A close-up photograph · the head or neck, leg and top or side of the foot are involved:
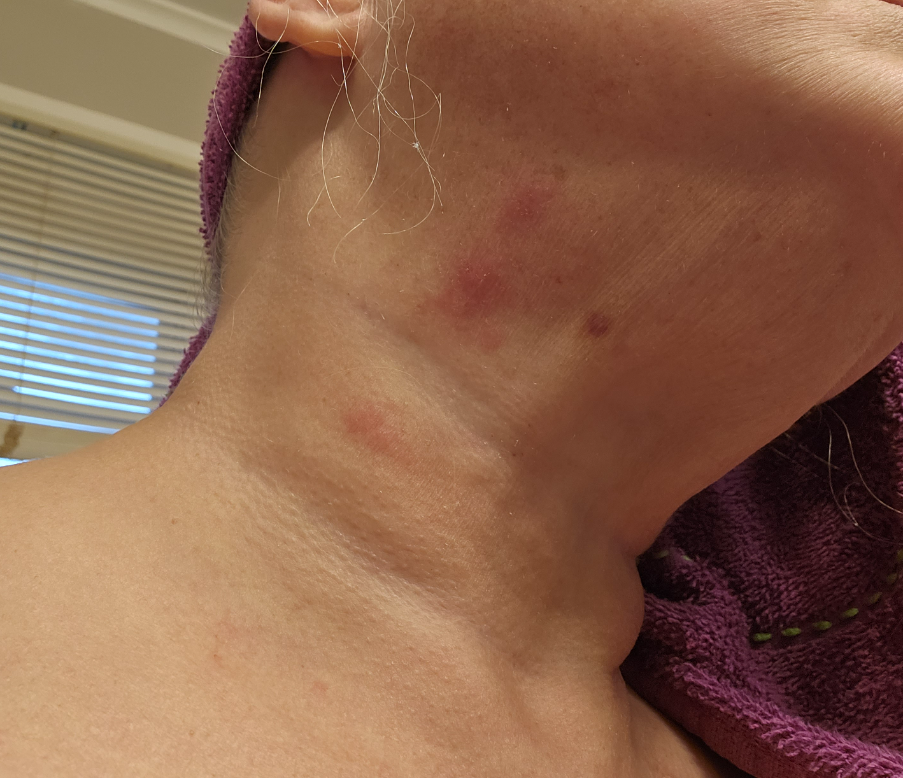Assessment:
On dermatologist assessment of the image: the differential, in no particular order, includes Allergic Contact Dermatitis and Irritant Contact Dermatitis.